Dermoscopy of a skin lesion · a female subject, in their mid-60s: 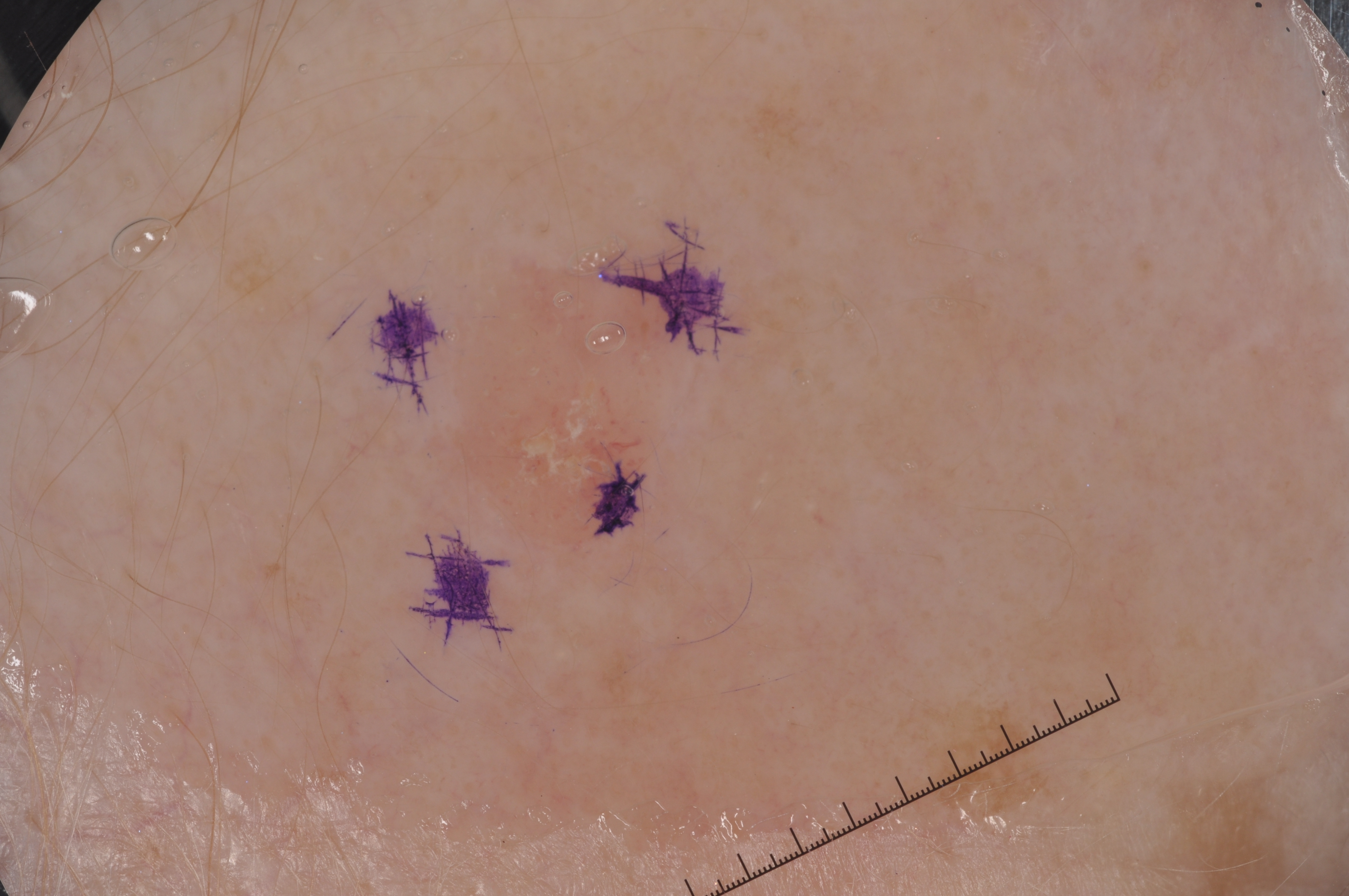Notes:
* extent — small
* features — milia-like cysts; absent: pigment network, negative network, and streaks
* lesion location — 443/266/695/546
* diagnosis — a seborrheic keratosis